The affected area is the arm and front of the torso; the photo was captured at an angle: 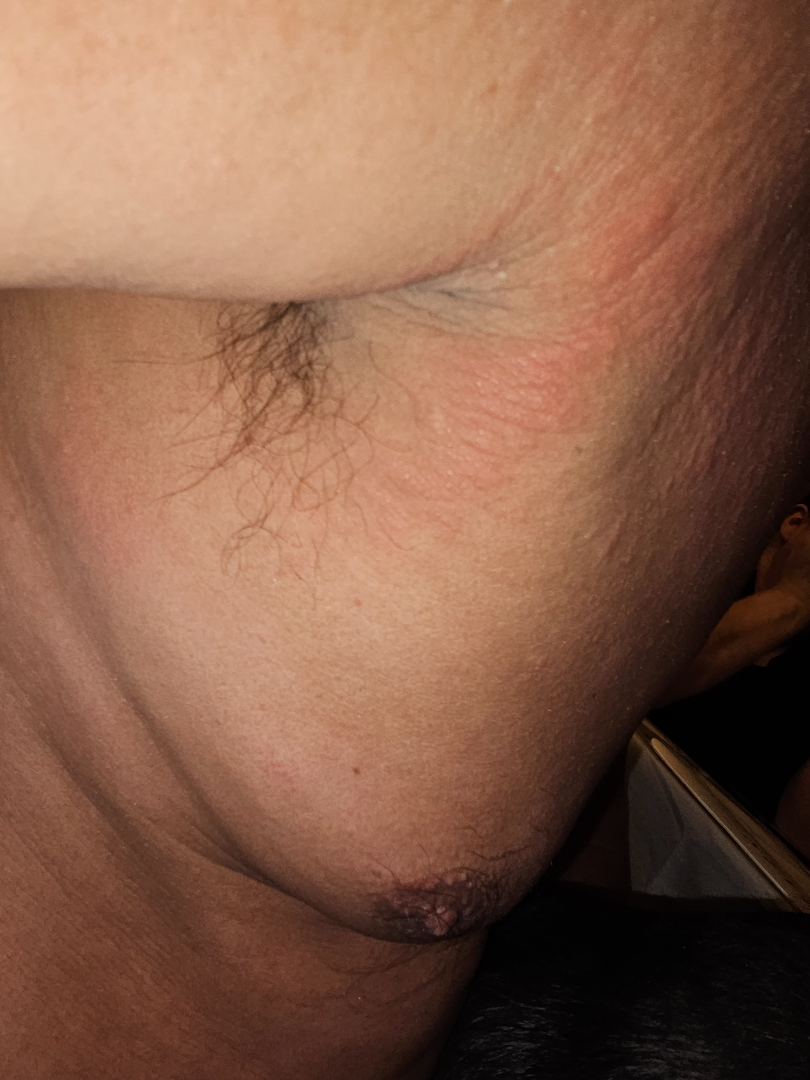Findings:
On photographic review by a dermatologist, Eczema (0.33); Hypersensitivity (0.33); Allergic Contact Dermatitis (0.33).